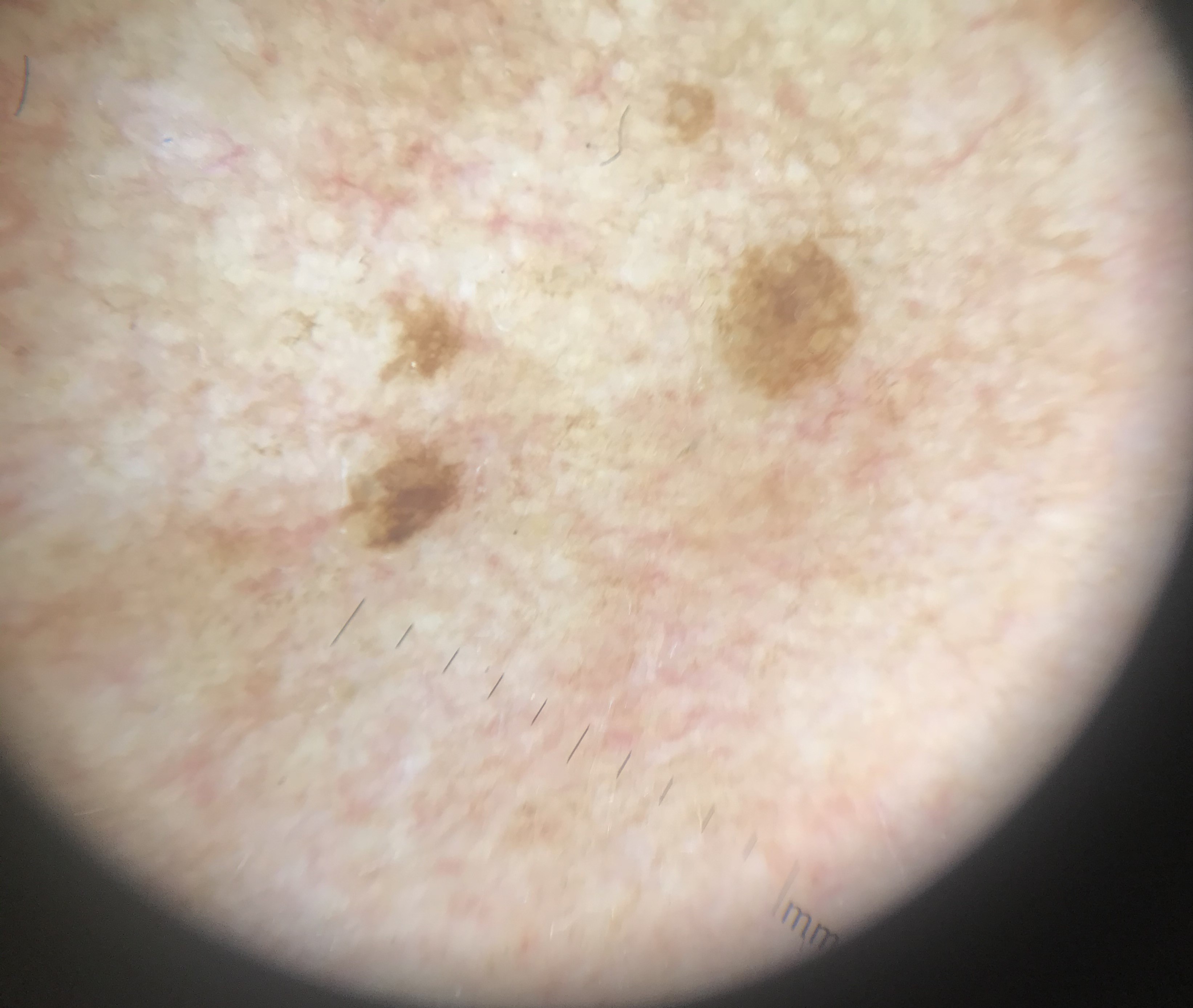Diagnosed as a seborrheic keratosis.